The affected area is the leg. The patient is 60–69, female. A close-up photograph.
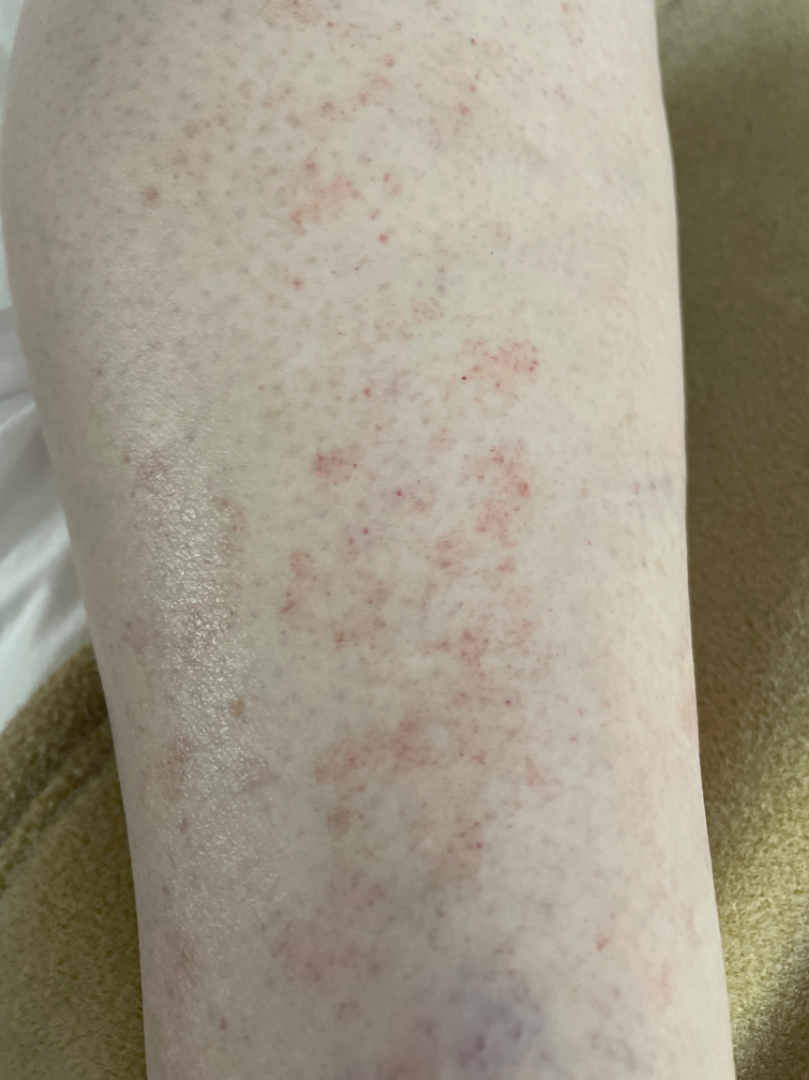Notes:
– clinical impression: Pigmented purpuric eruption (primary); Leukocytoclastic Vasculitis (lower probability)